Contact-polarized dermoscopy of a skin lesion. A female subject in their mid-50s. The patient was assessed as Fitzpatrick II — 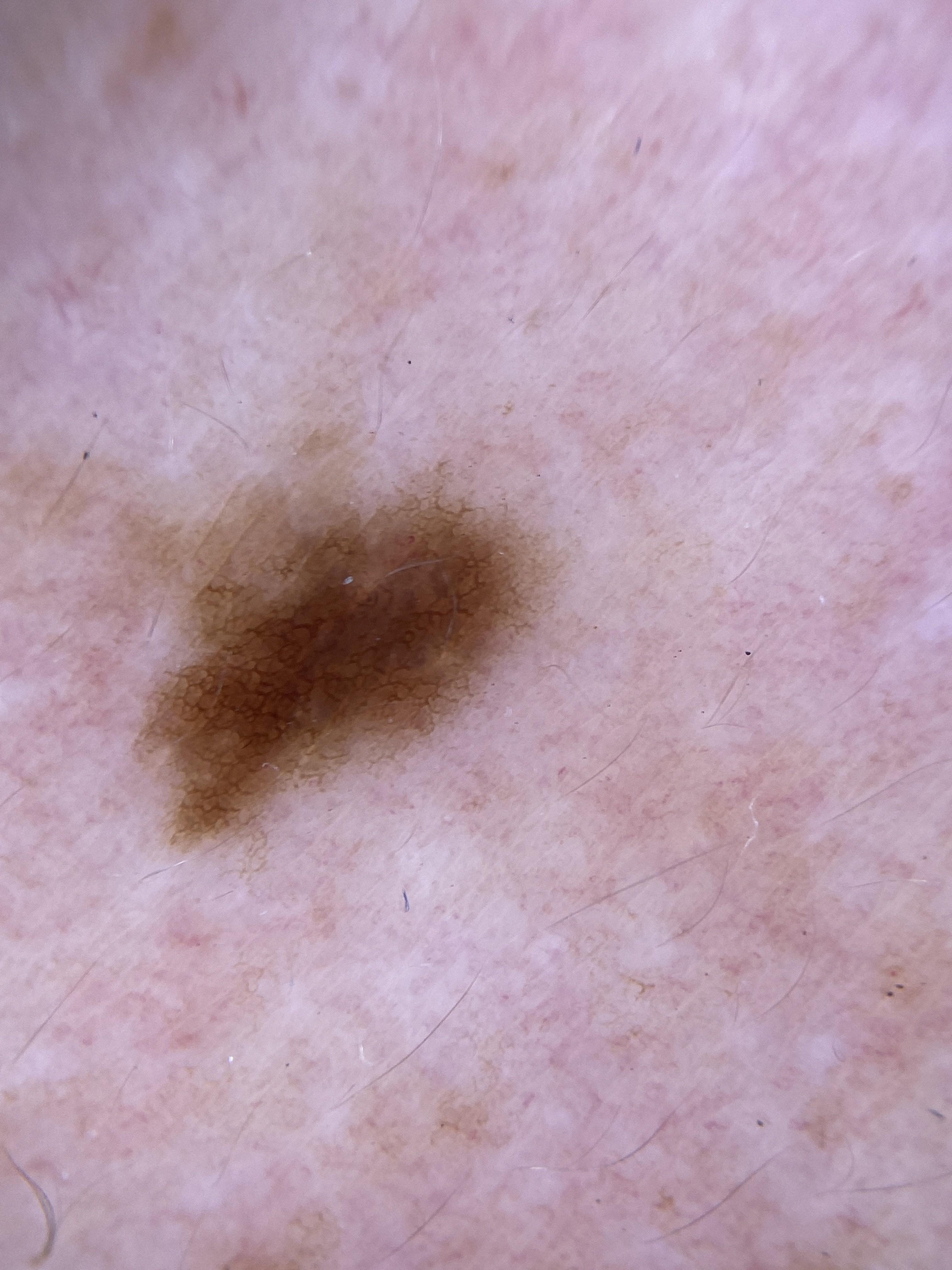The lesion was found on the anterior trunk. Clinically diagnosed as a benign, melanocytic lesion — a nevus.